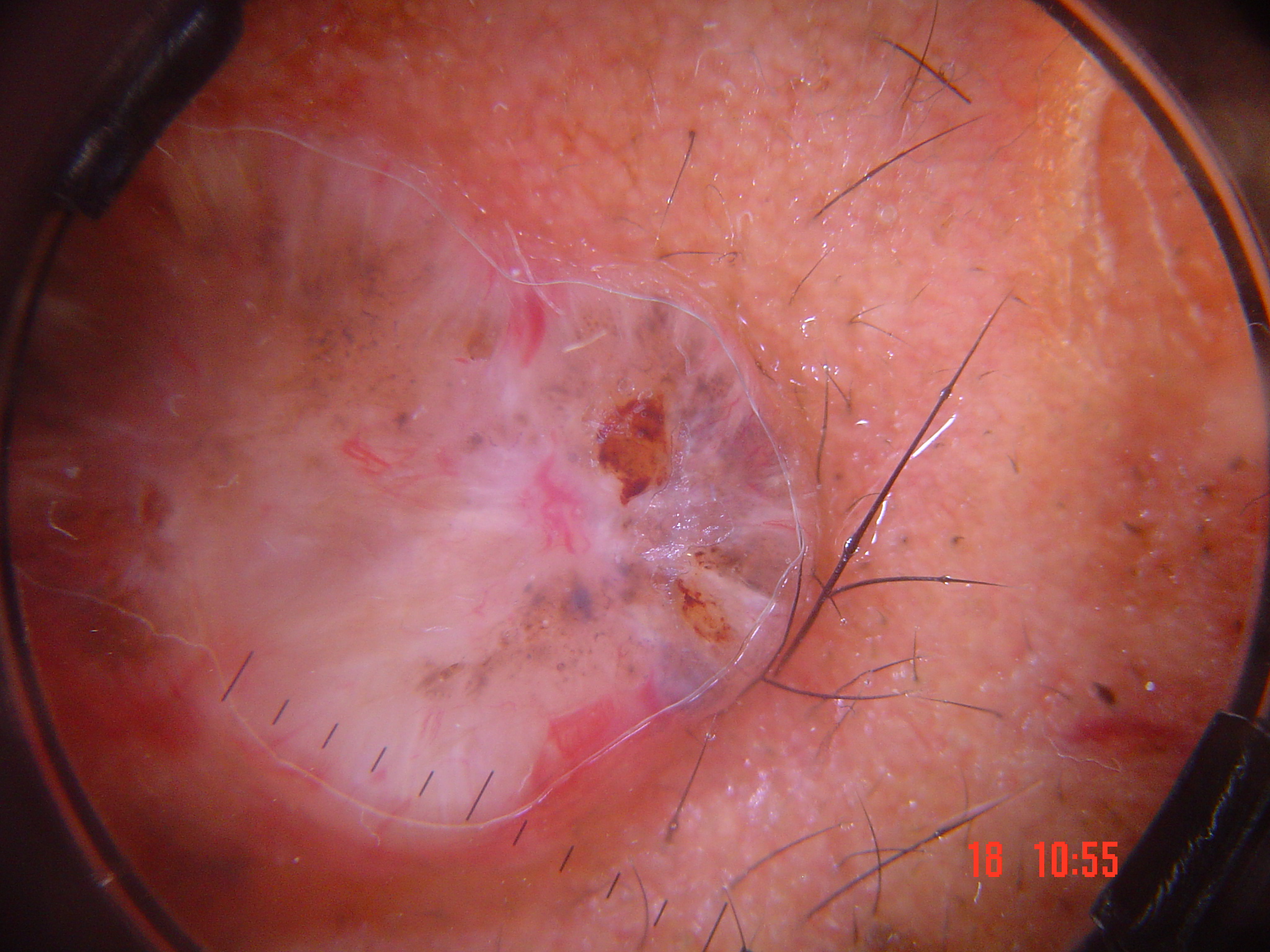image: dermoscopy; subtype: keratinocytic; diagnosis: basal cell carcinoma (biopsy-proven).